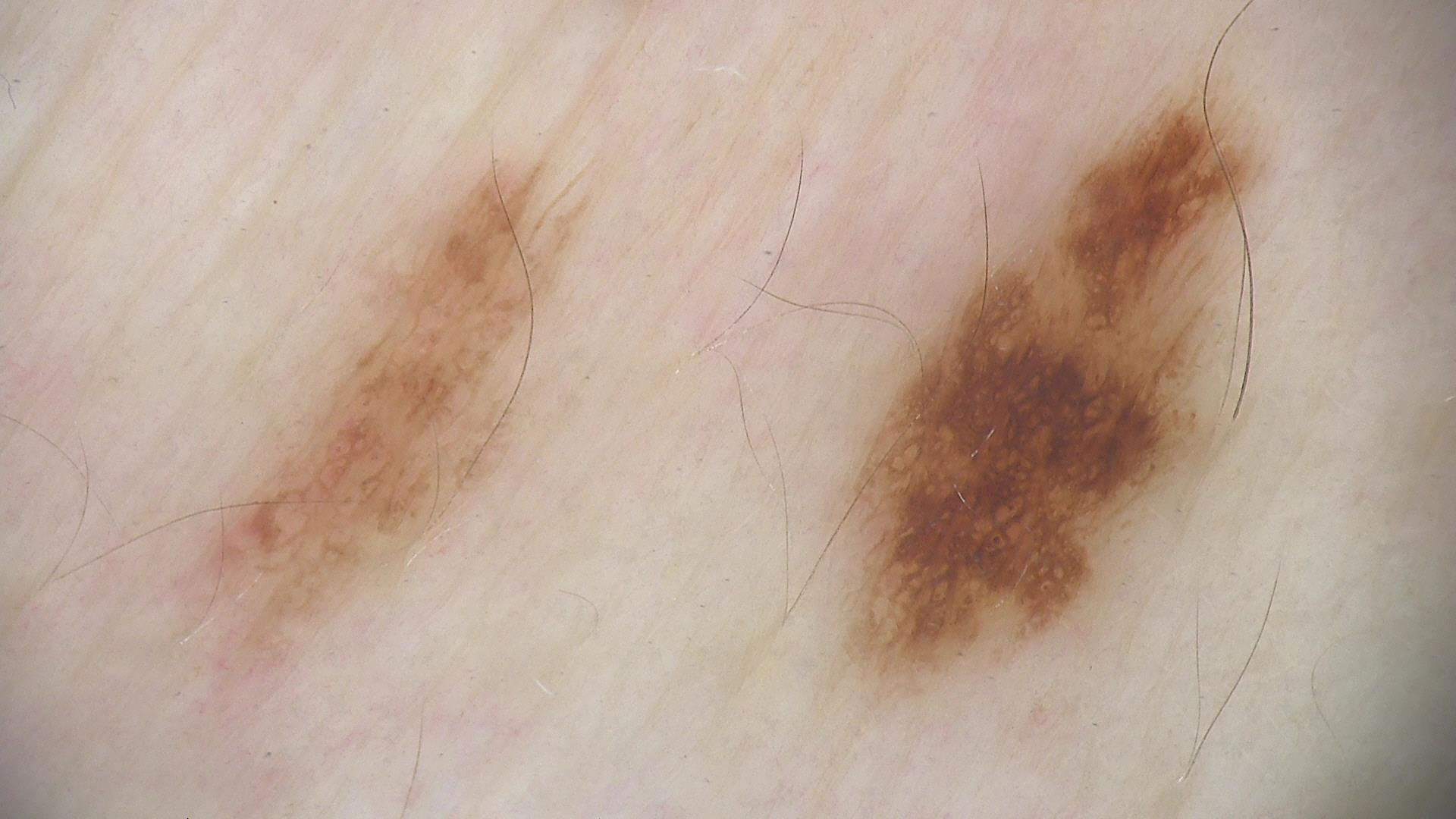diagnosis:
  name: dysplastic junctional nevus
  code: jd
  malignancy: benign
  super_class: melanocytic
  confirmation: expert consensus